A patient age 71; a smartphone photograph of a skin lesion.
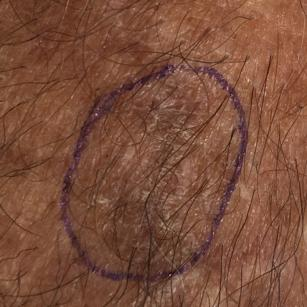• reported symptoms — itching, elevation, bleeding
• assessment — actinic keratosis (clinical consensus)